A skin lesion imaged with a dermatoscope:
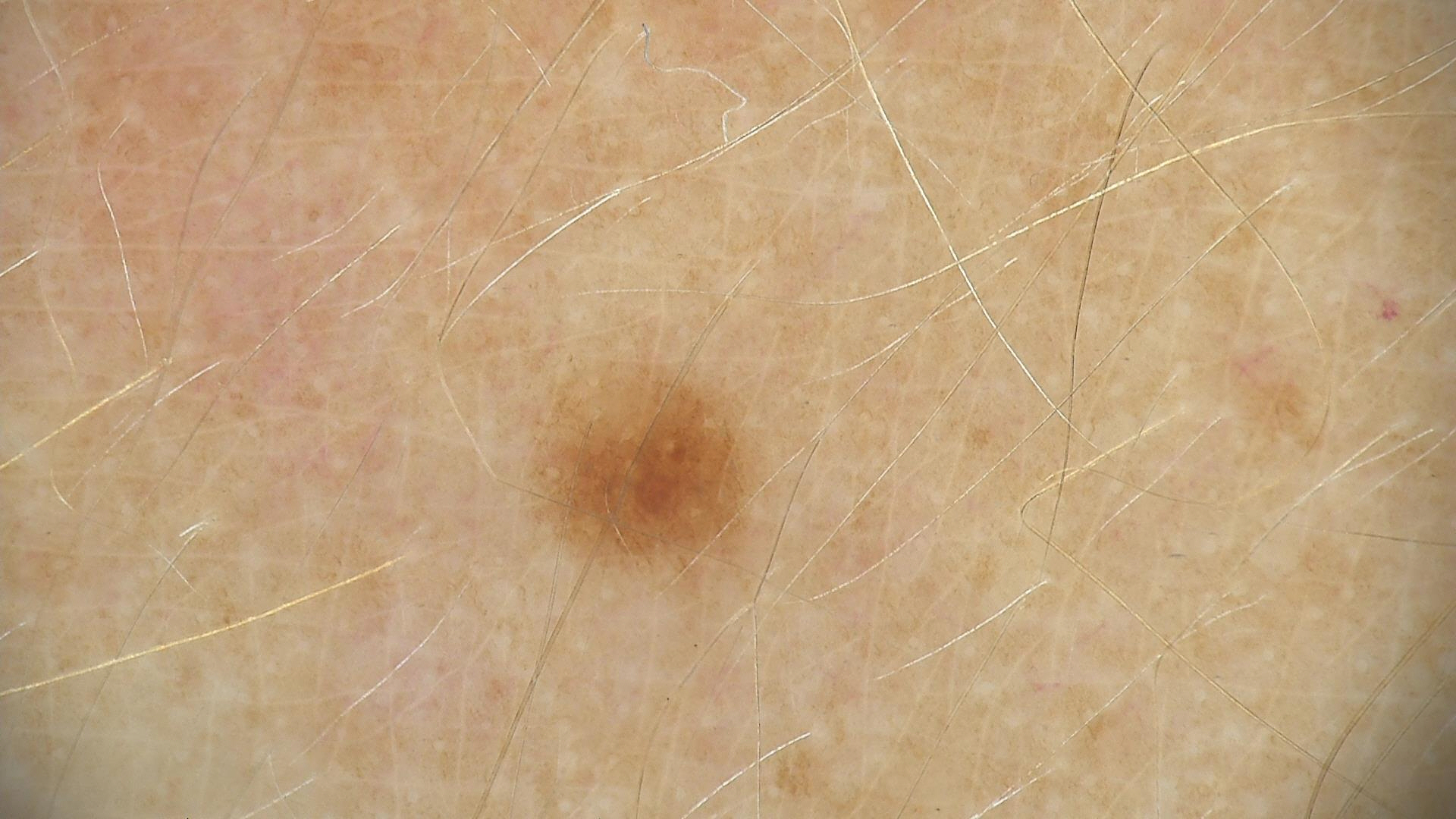Diagnosed as a benign lesion — a dysplastic junctional nevus.